Imaged for a research study, with no referral diagnosis recorded; the patient reports a personal history of skin cancer and a personal history of cancer; the patient says their skin tans without first burning; the patient describes having few moles overall; a dermoscopy image of a skin lesion; a female patient 60 years of age.
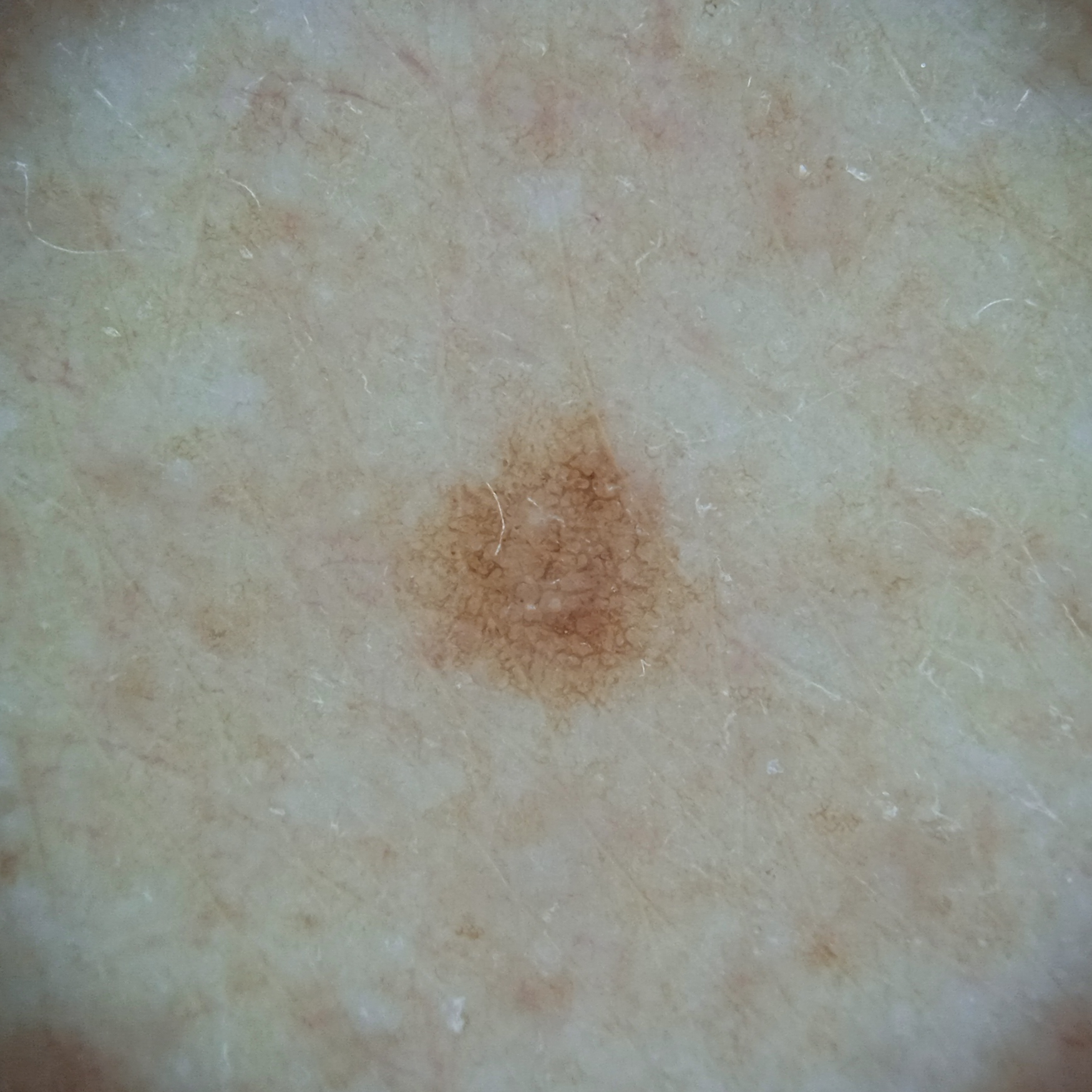| field | value |
|---|---|
| anatomic site | an arm |
| diameter | 2.8 mm |
| diagnostic label | melanocytic nevus (dermatologist consensus) |